A dermoscopic image of a skin lesion.
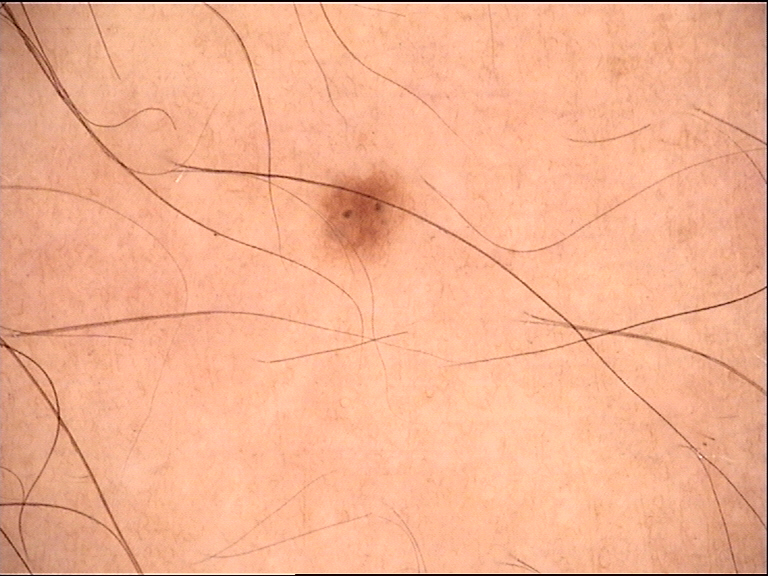Consistent with a dysplastic junctional nevus.